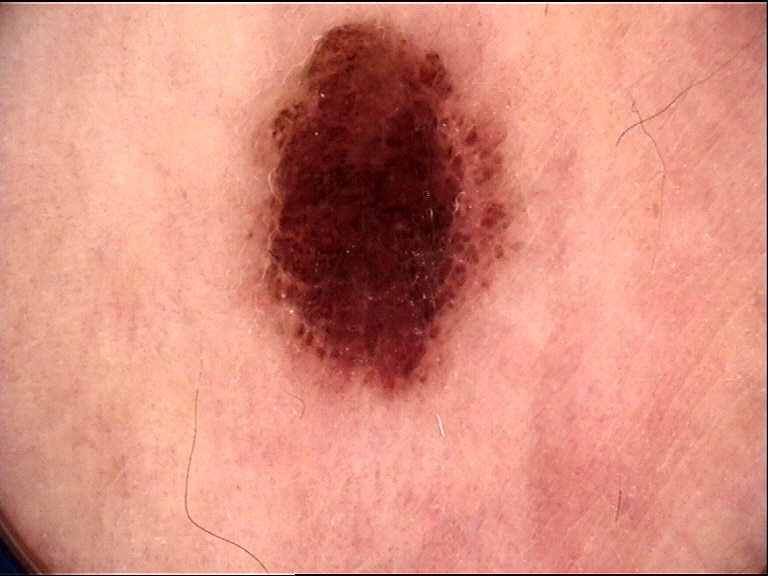imaging = dermatoscopy | label = compound nevus (expert consensus).